Present for about one day · the contributor is 18–29, female · texture is reported as raised or bumpy · Fitzpatrick III; non-clinician graders estimated Monk Skin Tone 2 or 3 (two reviewer pools) · the photo was captured at a distance · symptoms reported: itching and enlargement · the patient described the issue as a rash · the arm is involved · the patient reported no systemic symptoms: 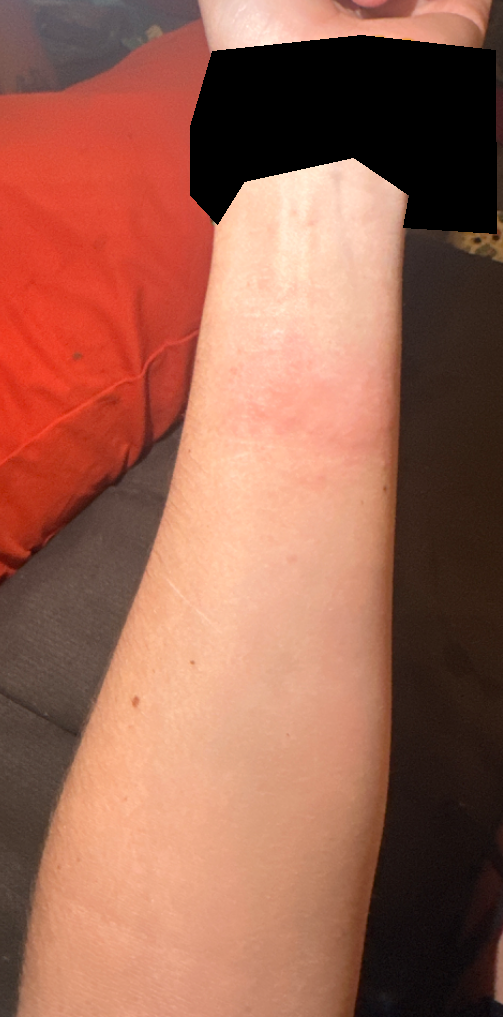Review:
The condition could not be reliably identified from the image.